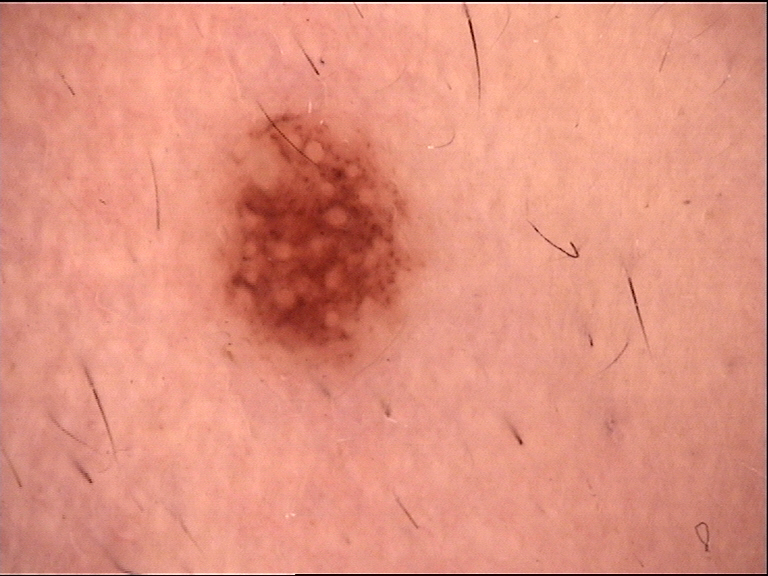A dermoscopic photograph of a skin lesion. Diagnosed as a compound nevus.